This image was taken at an angle, located on the arm:
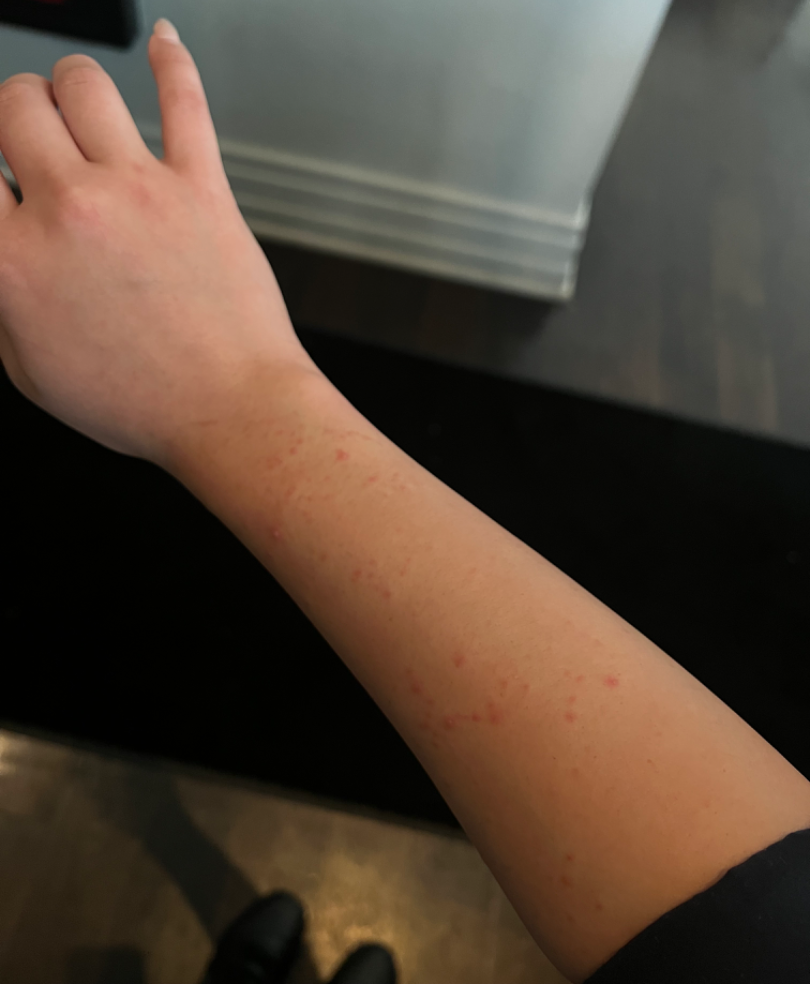differential diagnosis = most consistent with Folliculitis.